A clinical photograph showing a skin lesion. A subject age 67.
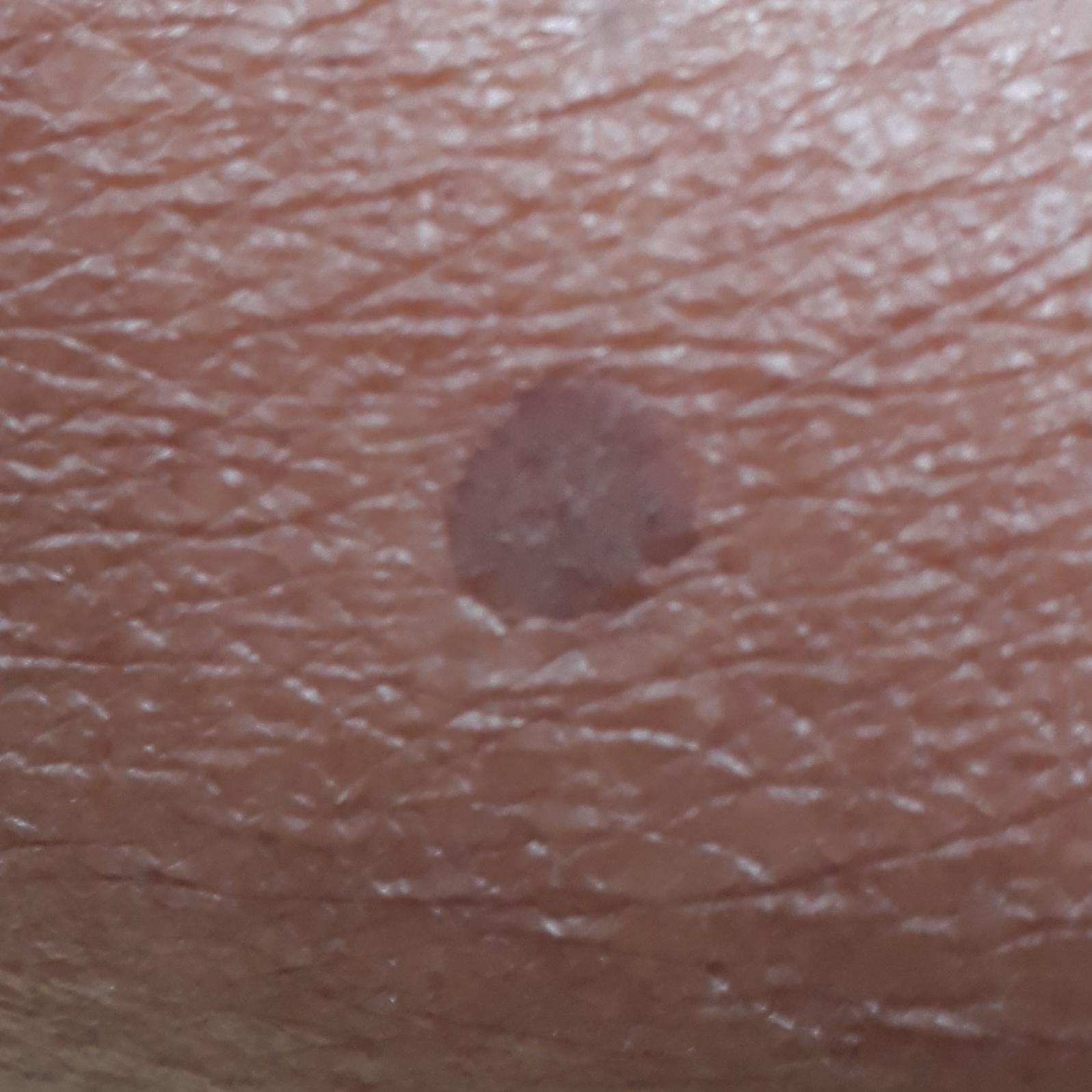The lesion is on a forearm. The patient reports no symptoms. Clinically diagnosed as a seborrheic keratosis.